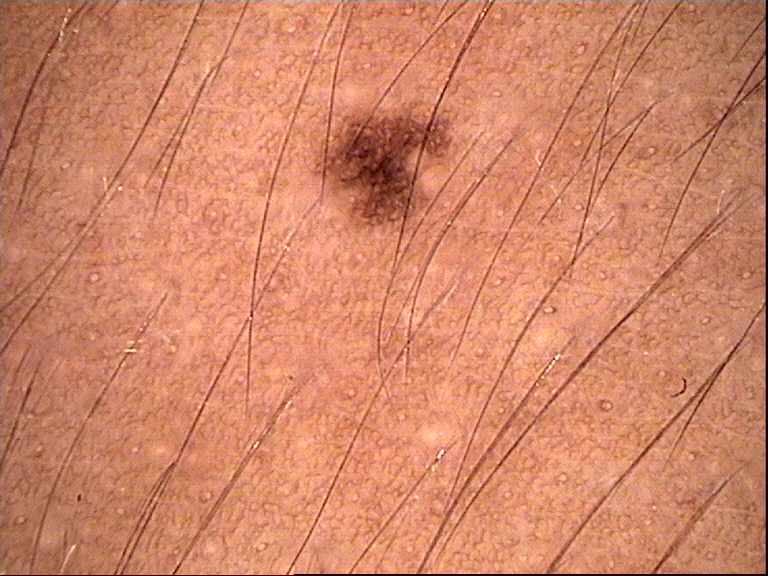A dermoscopy image of a single skin lesion. Consistent with a benign lesion — a dysplastic junctional nevus.